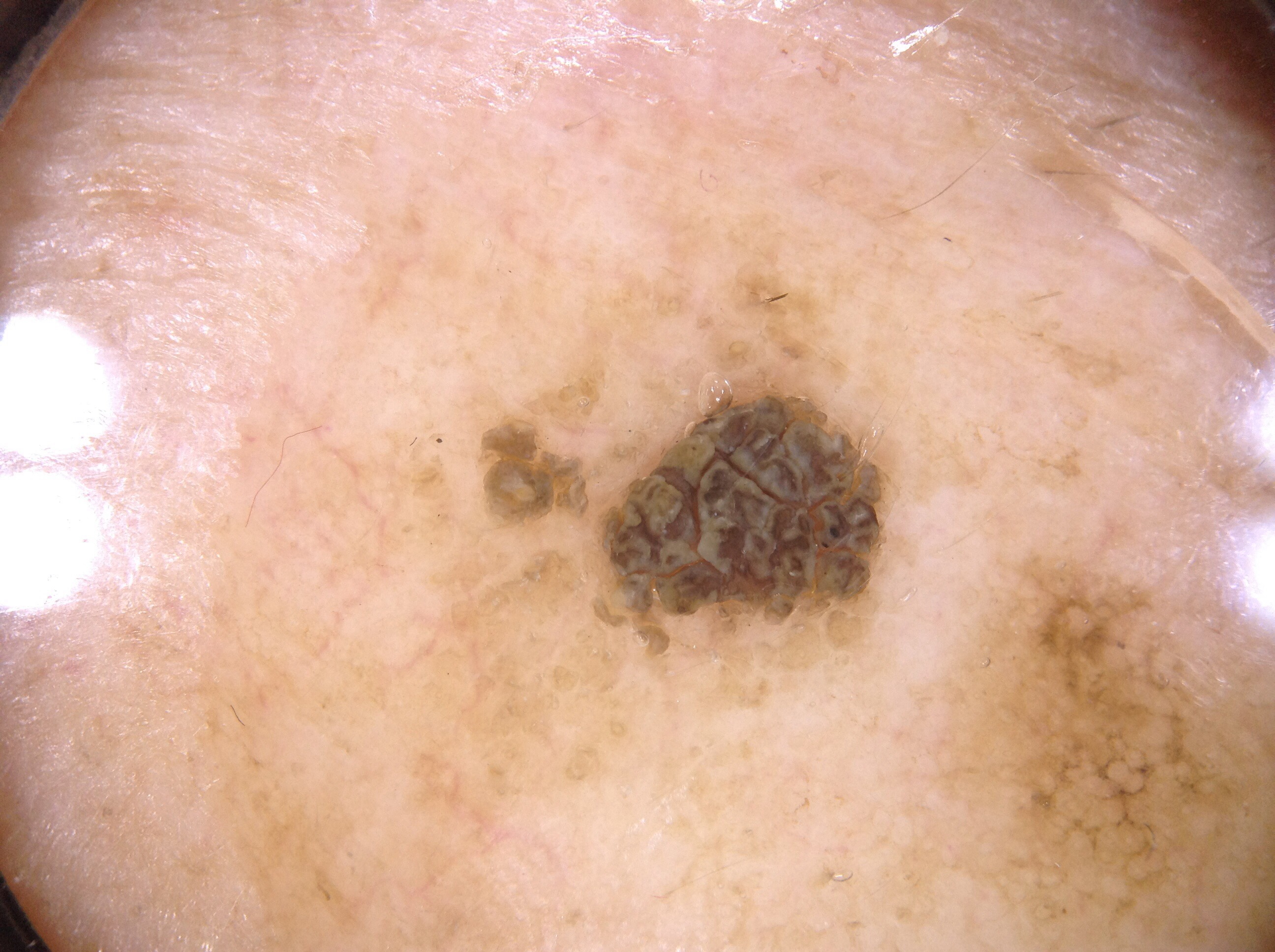Case summary: A skin lesion imaged with a dermatoscope. As (left, top, right, bottom), the lesion is bounded by [376,247,937,828]. Dermoscopic review identifies no milia-like cysts, pigment network, streaks, or negative network. Impression: Diagnosed as a seborrheic keratosis, a benign lesion.